The photo was captured at an angle; the lesion involves the back of the torso.
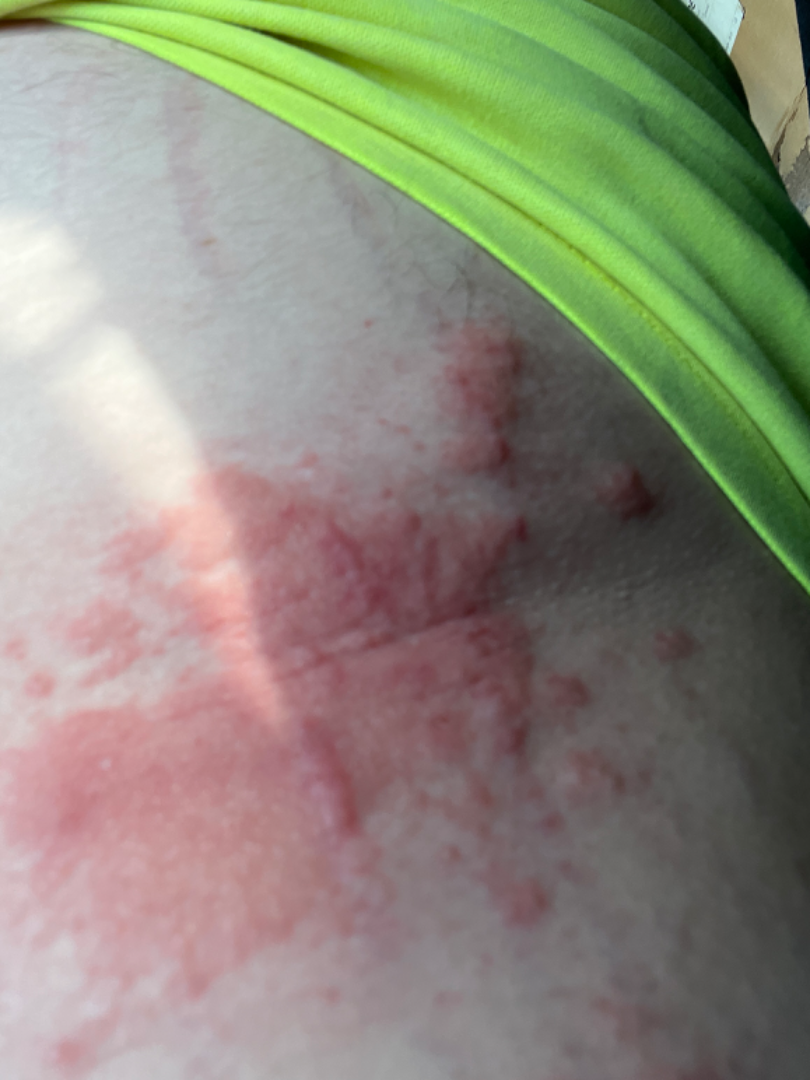Notes:
- assessment · indeterminate